This is a dermoscopic photograph of a skin lesion · a female subject, about 35 years old: 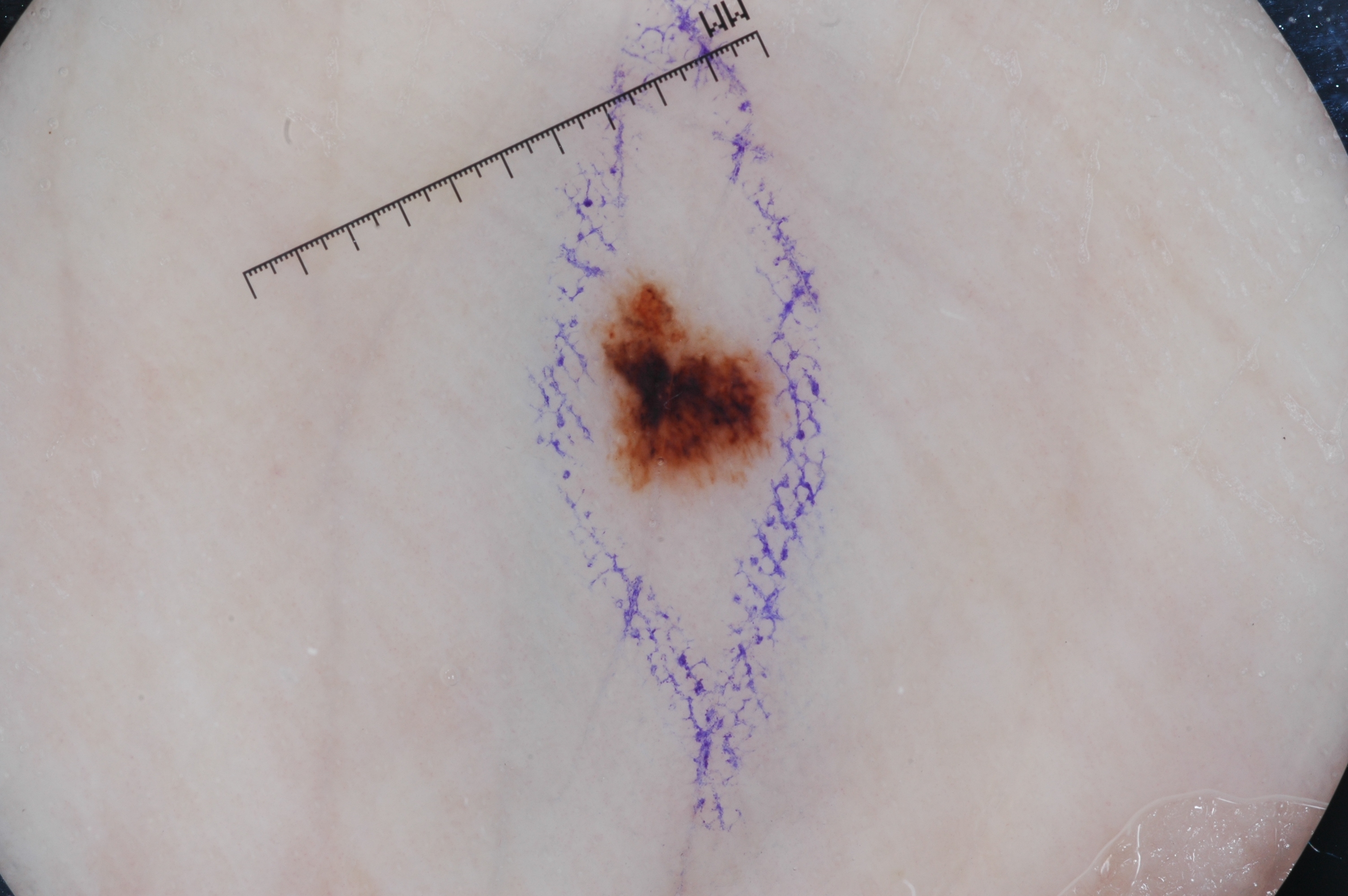Q: How large is the lesion within the image?
A: small
Q: What dermoscopic features are not present?
A: negative network, streaks, pigment network, and milia-like cysts
Q: Where is the lesion in the image?
A: 601 287 779 490
Q: What did the assessment conclude?
A: a melanocytic nevus, a benign skin lesion